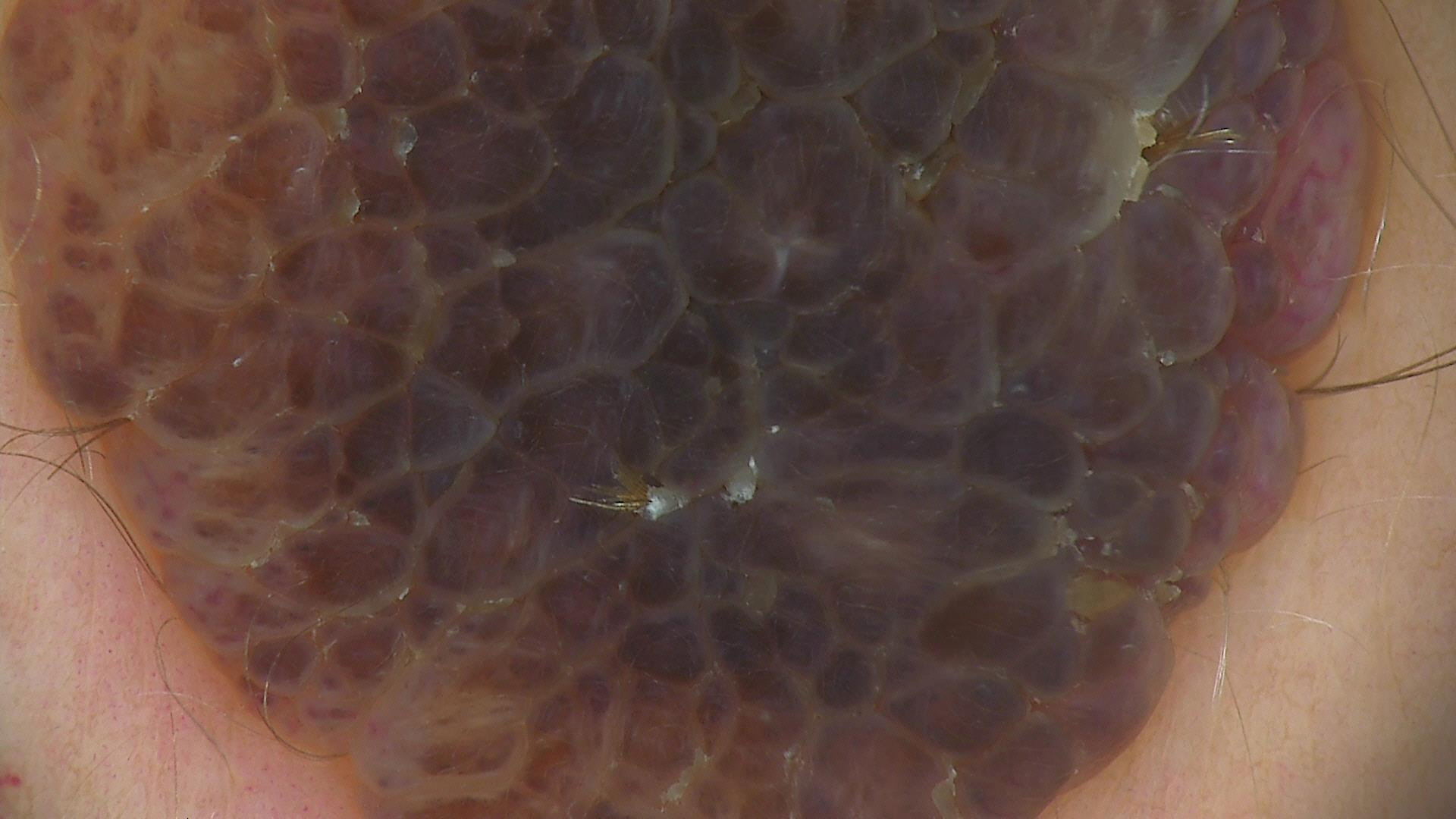image = dermatoscopy; assessment = congenital compound nevus (expert consensus).